The patient reports pain, enlargement, bleeding, itching, bothersome appearance and burning · the lesion is described as rough or flaky, raised or bumpy and fluid-filled · the arm is involved · self-categorized by the patient as skin that appeared healthy to them · the photograph was taken at an angle · the subject is a male aged 40–49 · the patient reports the condition has been present for one to four weeks · the patient reports associated fever, fatigue, shortness of breath, joint pain and chills: 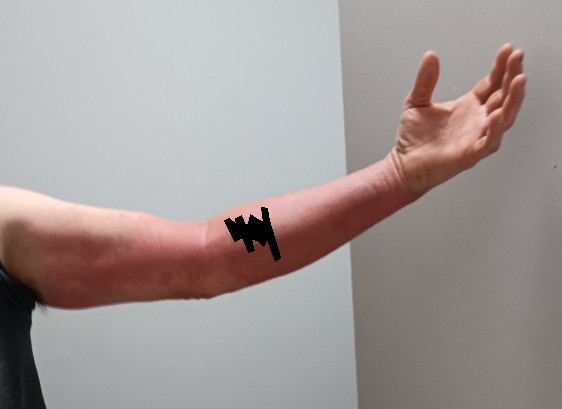Most likely Cutaneous lupus.